Dermoscopy of a skin lesion.
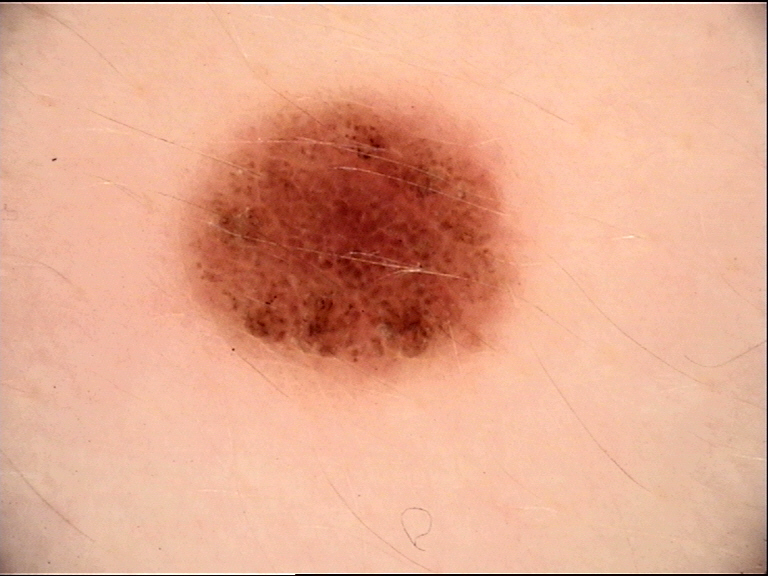Findings:
The architecture is that of a banal lesion.
Conclusion:
The diagnostic label was a compound nevus.